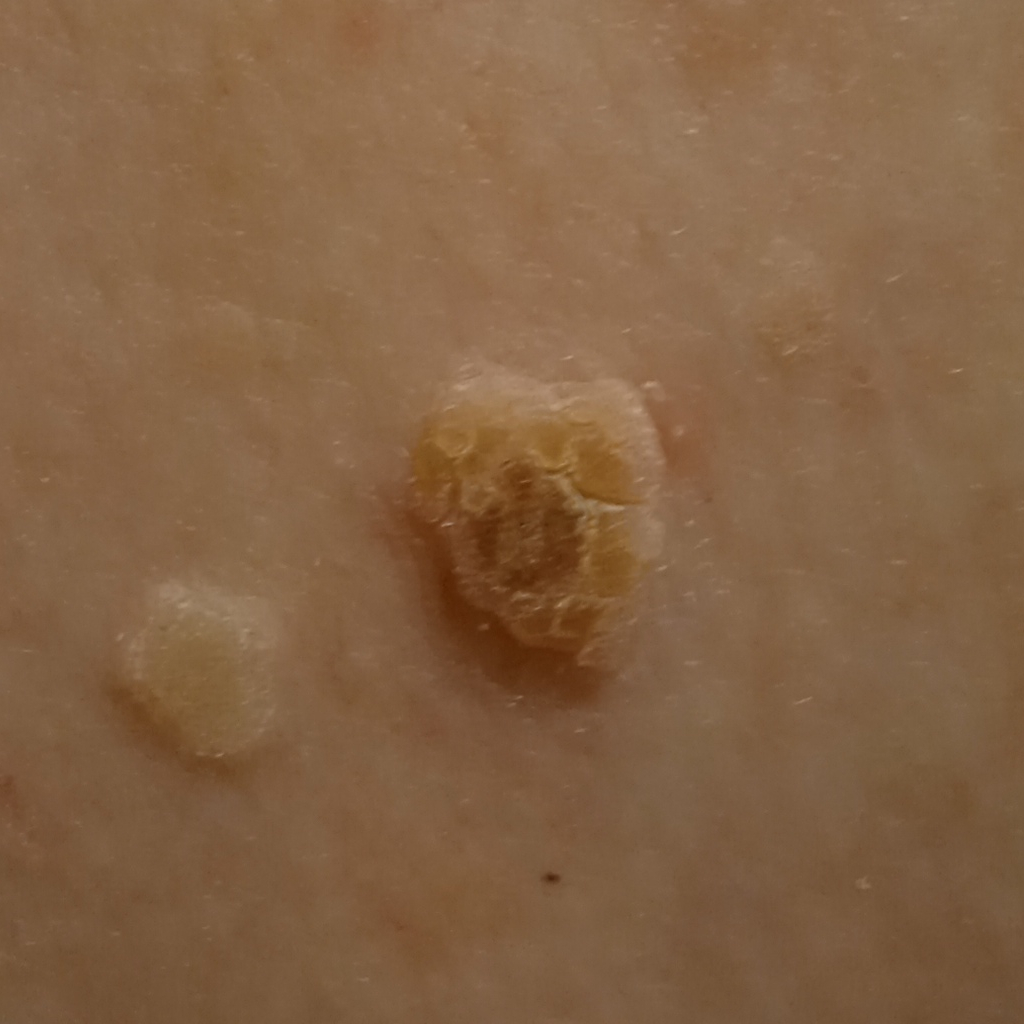{"risk_factors": {"positive": ["a personal history of cancer", "a personal history of skin cancer"]}, "referral": "research study (no referral diagnosis)", "image": "clinical photo", "mole_burden": "a moderate number of melanocytic nevi", "patient": {"age": 77, "sex": "male"}, "sun_reaction": "skin reddens with sun exposure", "lesion_location": "the back", "lesion_size": {"diameter_mm": 11.1}, "diagnosis": {"name": "actinic keratosis", "malignancy": "benign"}}